A dermoscopy image of a skin lesion; imaged for a research study, with no referral diagnosis recorded: 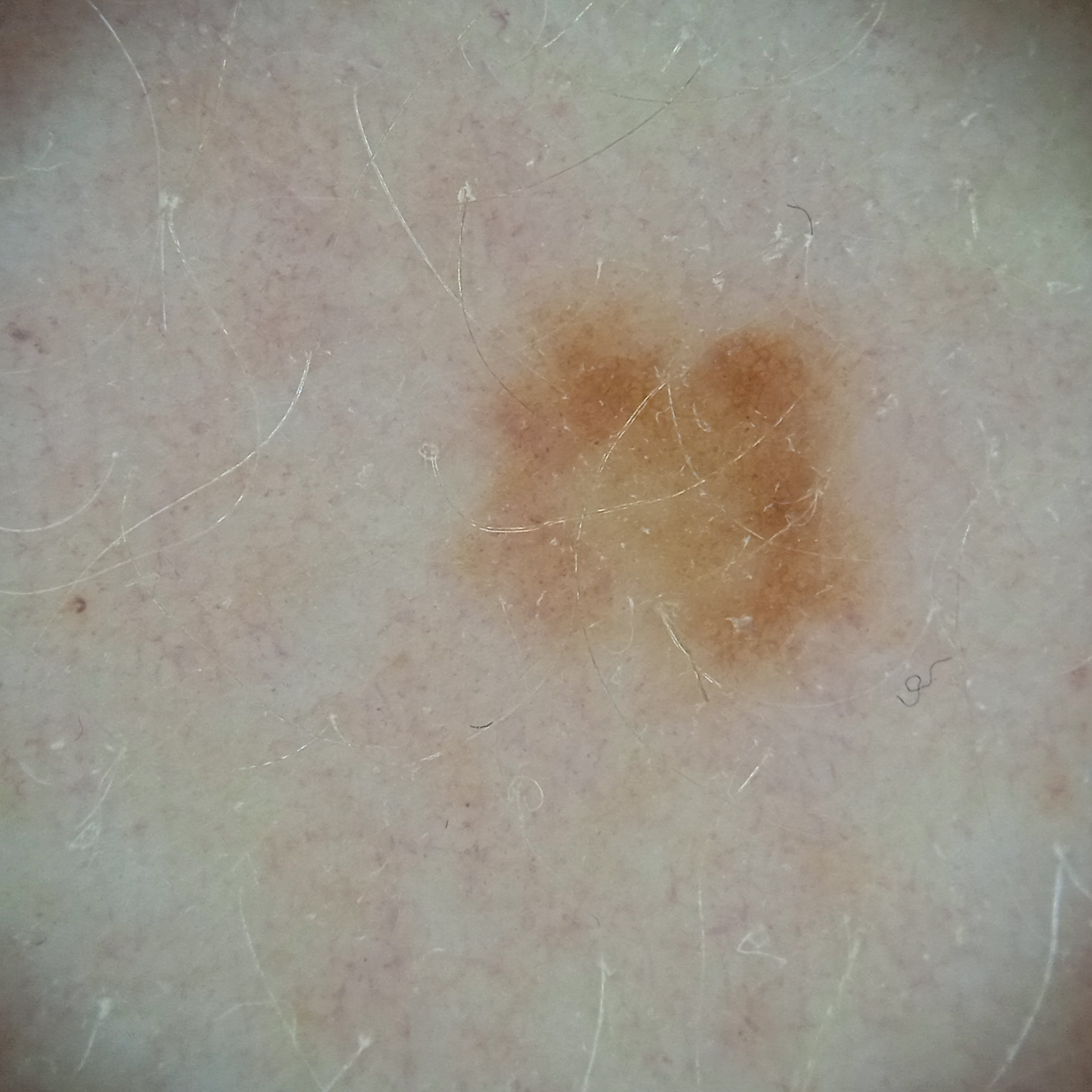Case summary: The lesion is located on an arm. Measuring roughly 4.7 mm. Impression: Dermatologist review favored an atypical (dysplastic) nevus.